A dermatoscopic image of a skin lesion; a male patient aged 78 to 82 — 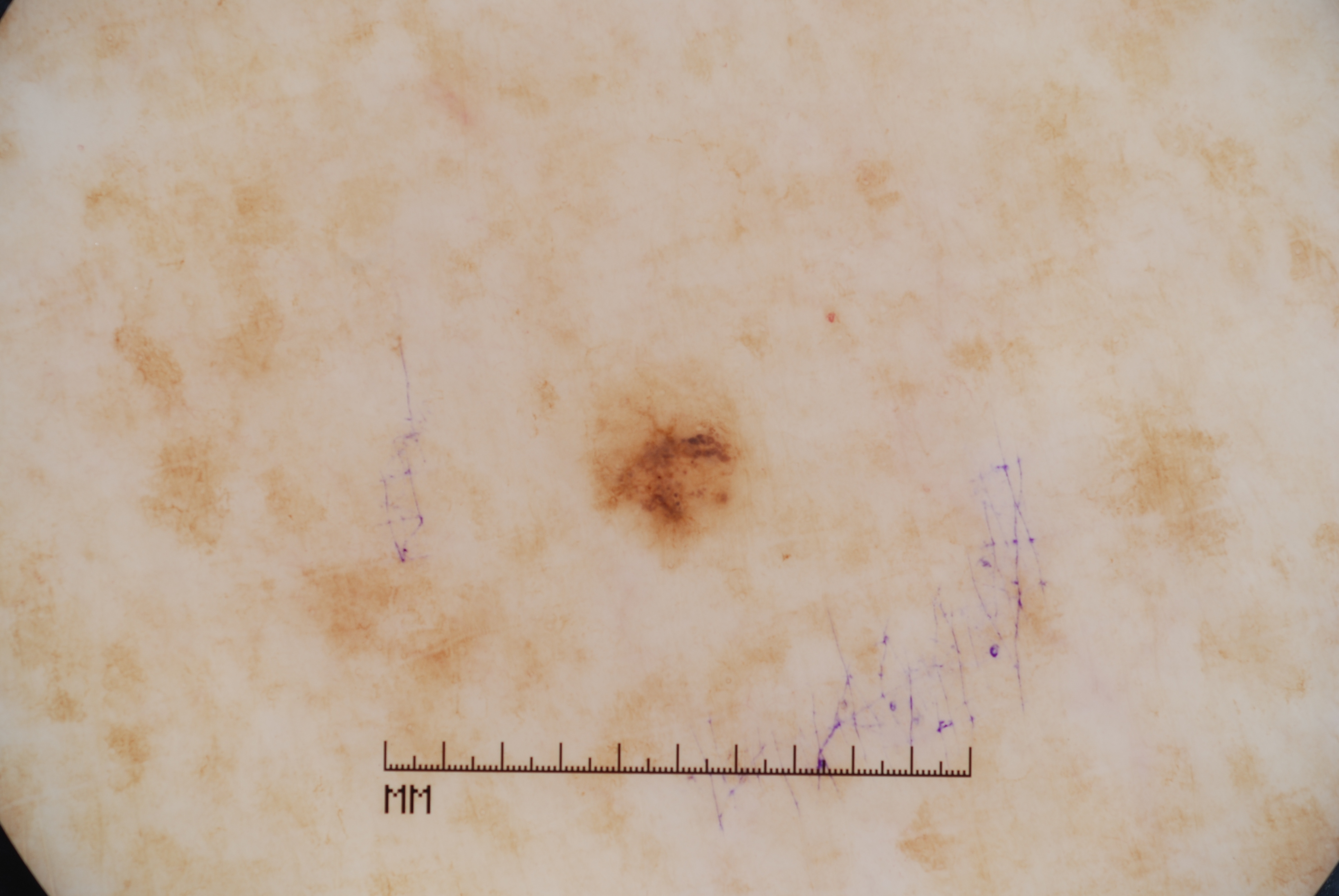The lesion takes up about 2% of the image. Lesion location: [586,371,753,539]. On dermoscopy, the lesion shows pigment network, with no milia-like cysts, negative network, or streaks. Clinically diagnosed as a melanocytic nevus, a benign skin lesion.